The leg is involved; this is a close-up image.
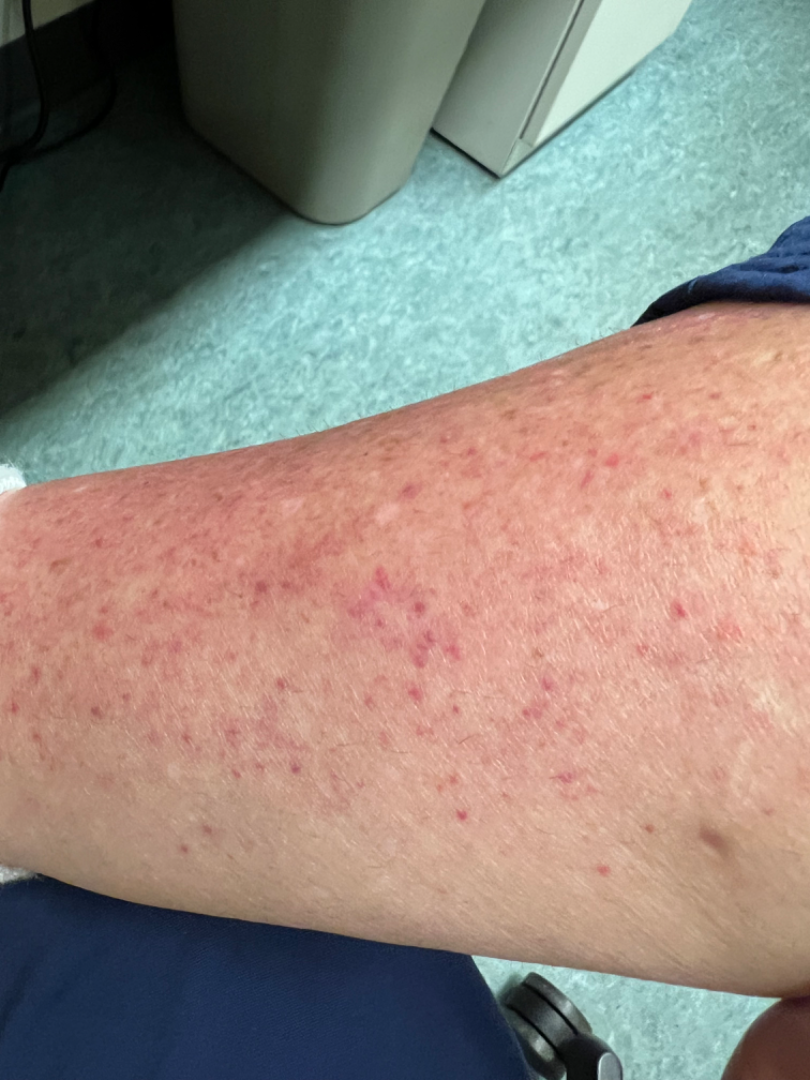Findings:
• assessment — indeterminate
• symptoms — itching
• lesion texture — raised or bumpy